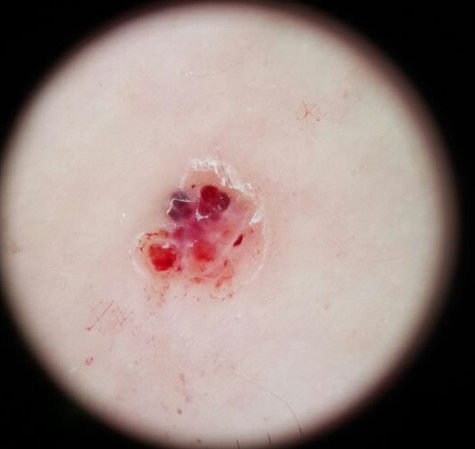– assessment: angiokeratoma (expert consensus)